The patient describes having few moles overall. Collected as part of a research study, without a referral diagnosis. The patient says their skin reddens with sun exposure: 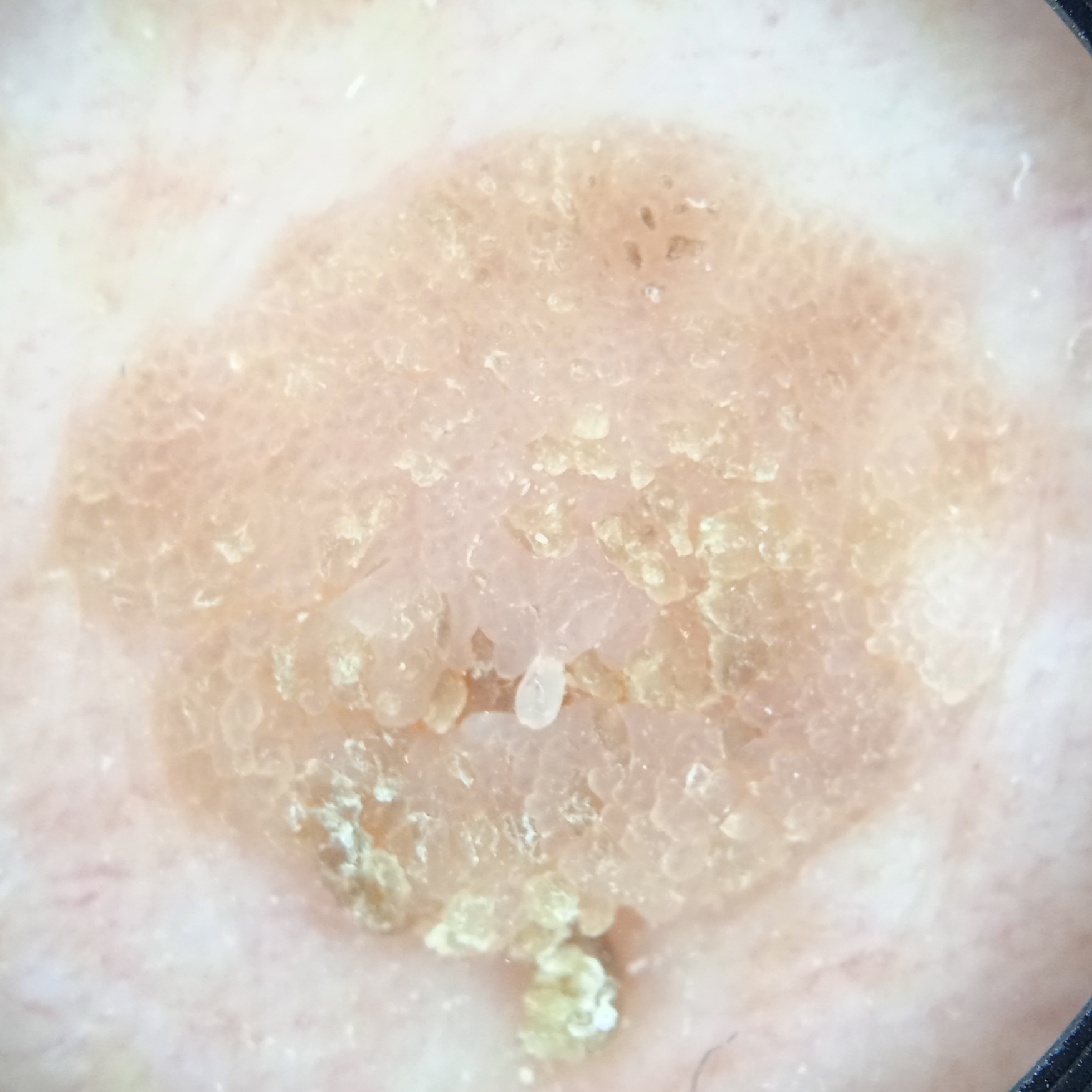anatomic site: the torso; diagnosis: seborrheic keratosis (dermatologist consensus).